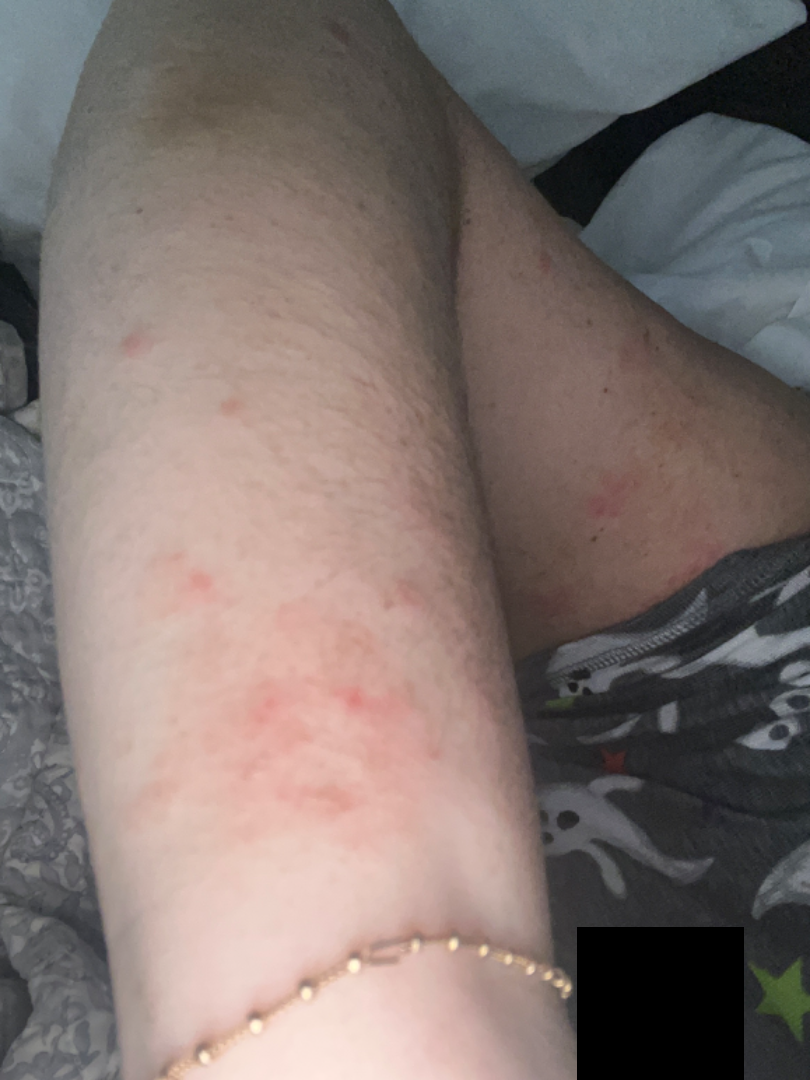Q: What conditions are considered?
A: the impression was split between Impetigo; Photodermatitis; and Acute dermatitis, NOS